The patient also reports fatigue. An image taken at an angle. Reported lesion symptoms include burning and itching. The lesion involves the leg and arm. The patient described the issue as a rash. Present for one to four weeks — 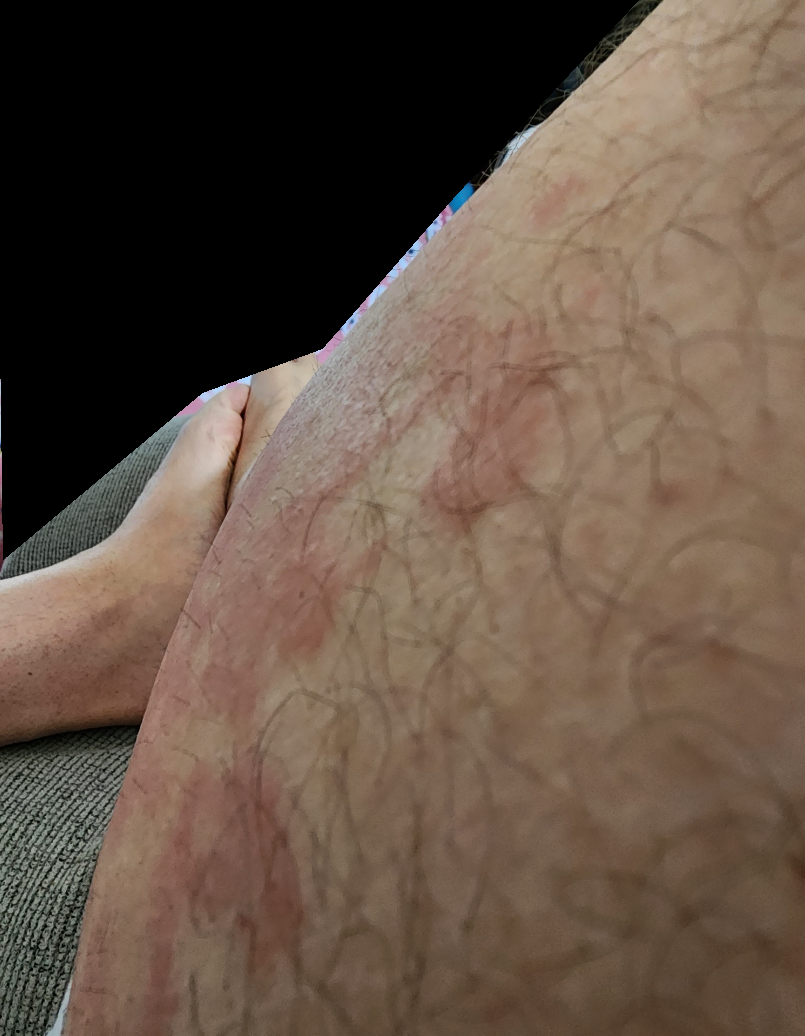Most likely Urticaria; also consider Granuloma annulare; also raised was Cutaneous lupus.